A clinical photograph of a skin lesion · a subject age 50.
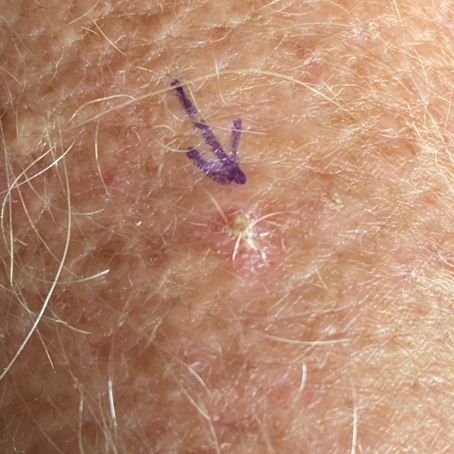Patient and lesion: By the patient's account, the lesion is elevated and itches, but has not changed. Conclusion: The diagnostic impression was an actinic keratosis.